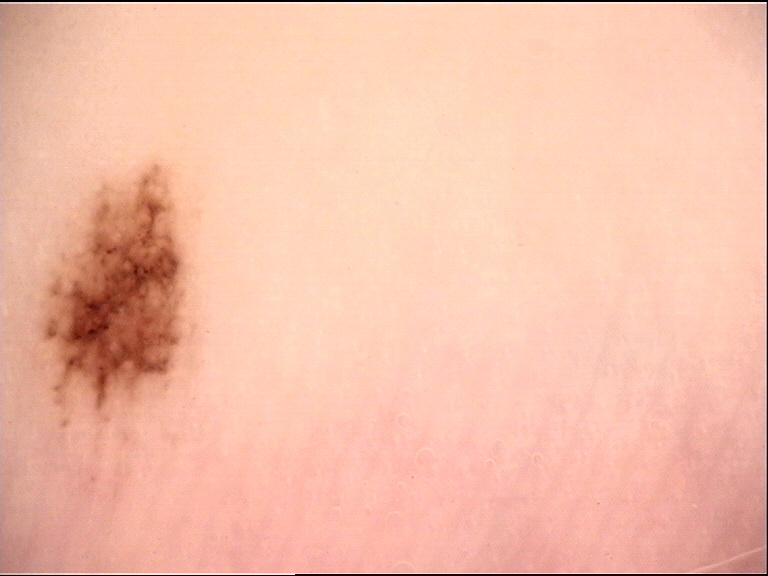Summary:
A dermoscopic image of a skin lesion.
Impression:
Consistent with an acral dysplastic junctional nevus.